A female patient approximately 35 years of age; Fitzpatrick II — 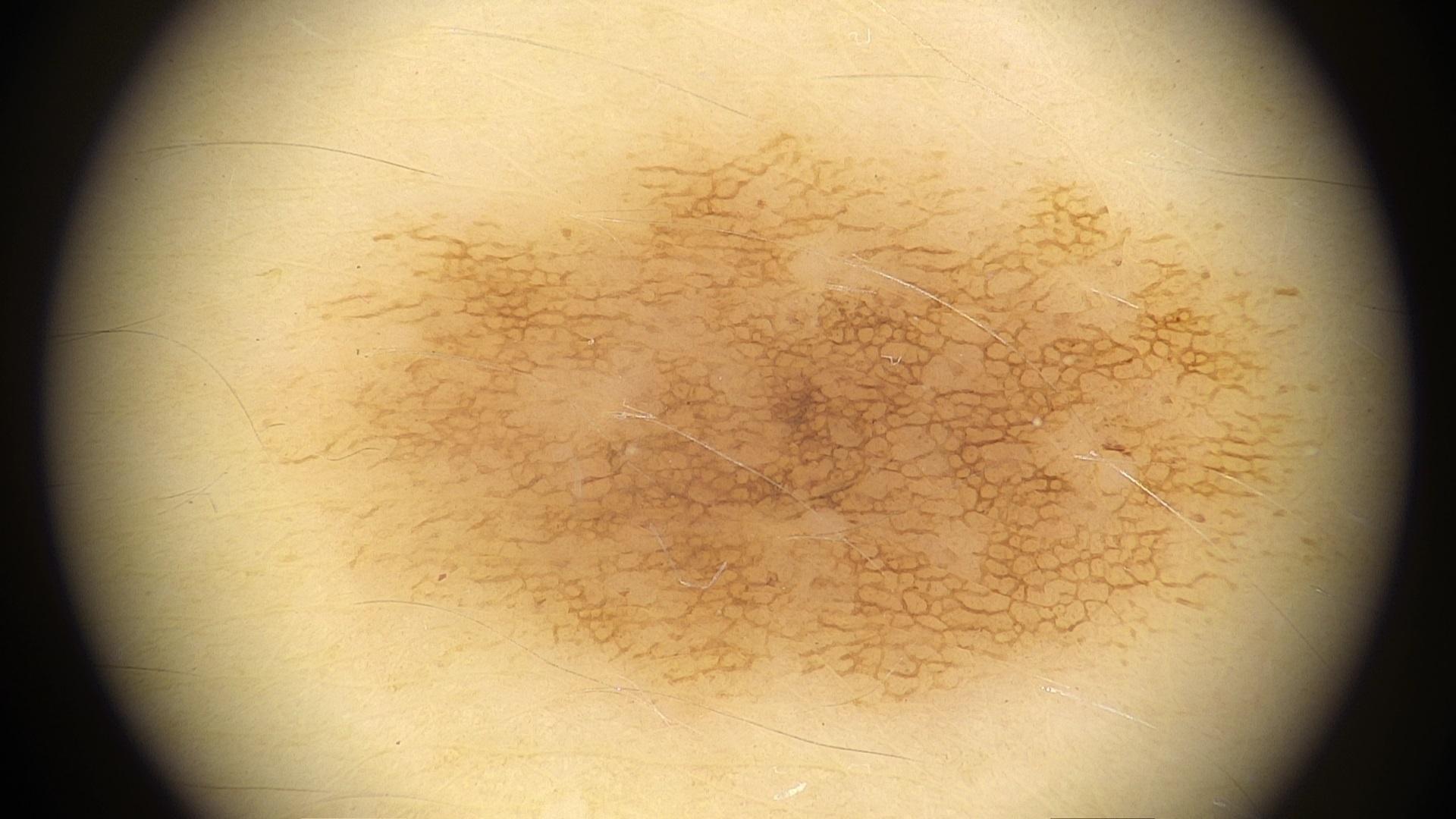Clinical context:
The lesion was found on the trunk.
Assessment:
Clinically diagnosed as a lesion of melanocytic lineage — a nevus.